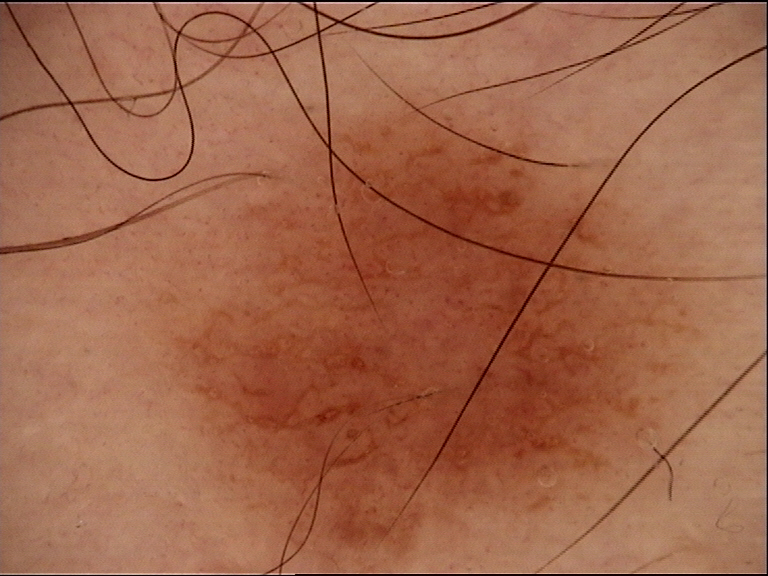image — dermatoscopy
diagnosis — dysplastic junctional nevus (expert consensus)